The contributor reports itching; located on the front of the torso and back of the torso; the photograph was taken at a distance:
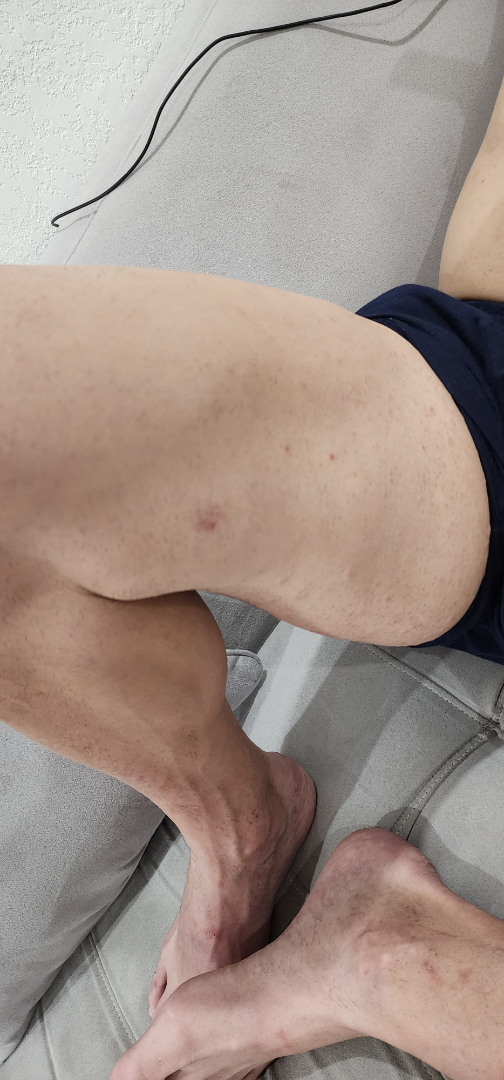On dermatologist assessment of the image, most consistent with Folliculitis.